A skin lesion imaged with a dermatoscope:
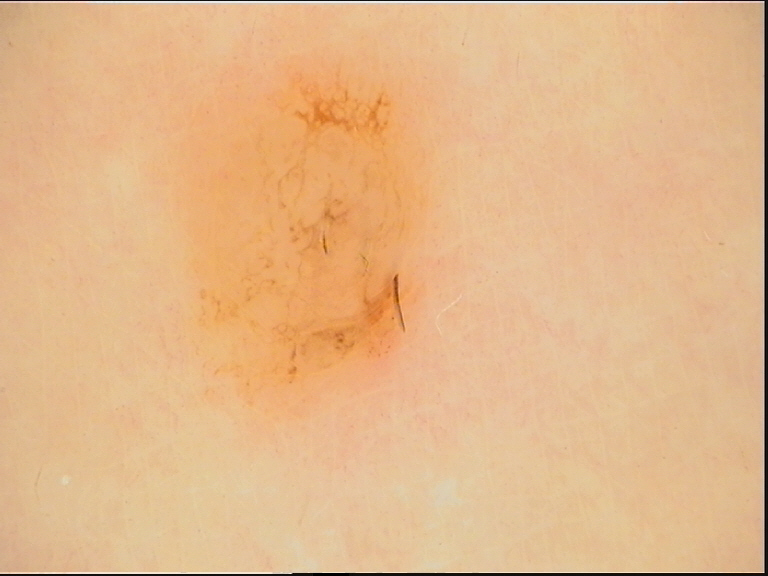Labeled as a junctional nevus.